A dermoscopy image of a single skin lesion:
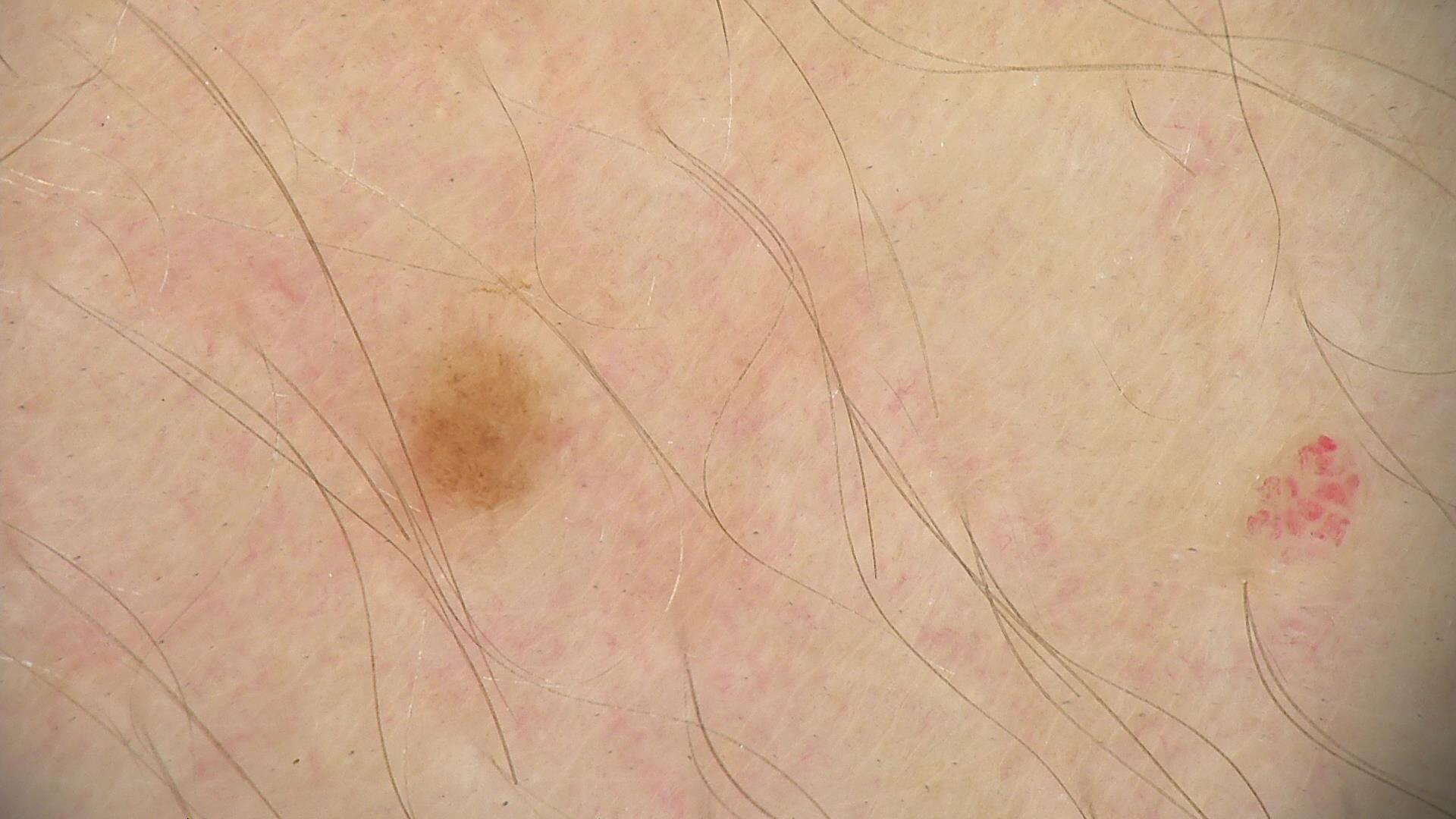<case>
  <diagnosis>
    <name>dysplastic junctional nevus</name>
    <code>jd</code>
    <malignancy>benign</malignancy>
    <super_class>melanocytic</super_class>
    <confirmation>expert consensus</confirmation>
  </diagnosis>
</case>